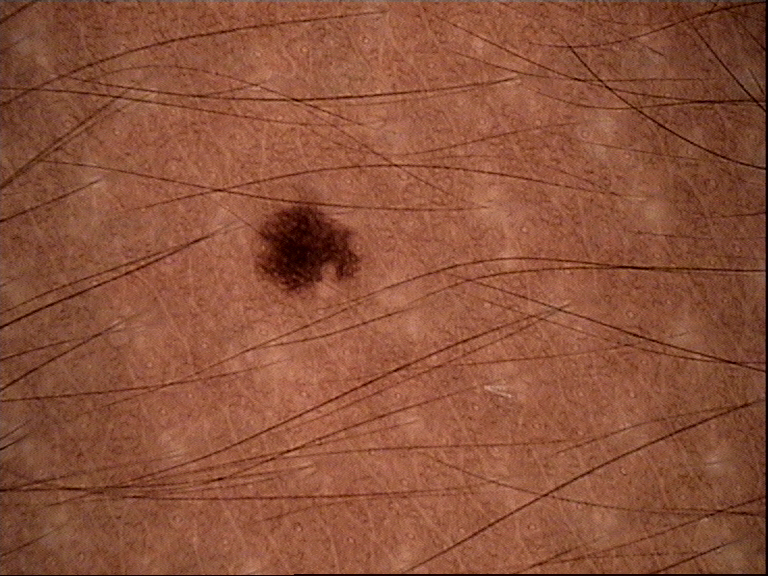Q: How is the lesion classified?
A: banal
Q: What was the diagnostic impression?
A: junctional nevus (expert consensus)